A dermoscopy image of a single skin lesion.
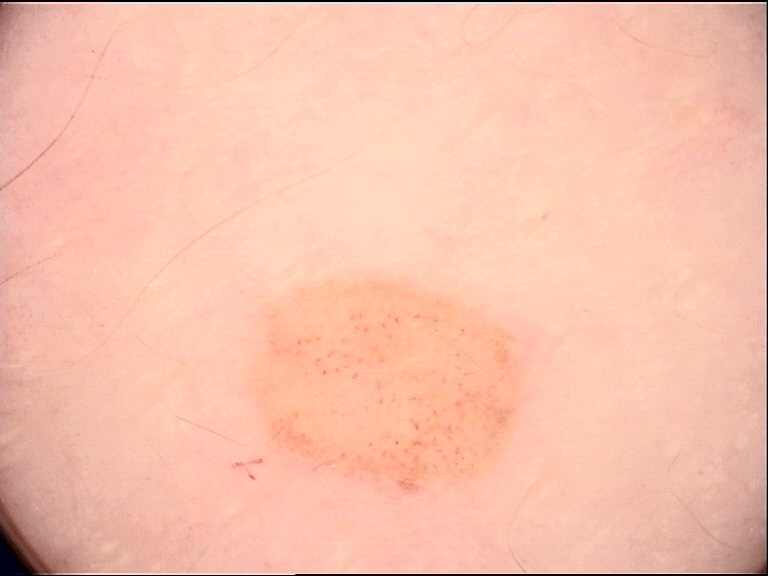{"lesion_type": {"main_class": "banal", "pattern": "compound"}, "diagnosis": {"name": "compound nevus", "code": "cb", "malignancy": "benign", "super_class": "melanocytic", "confirmation": "expert consensus"}}